A dermatoscopic image of a skin lesion.
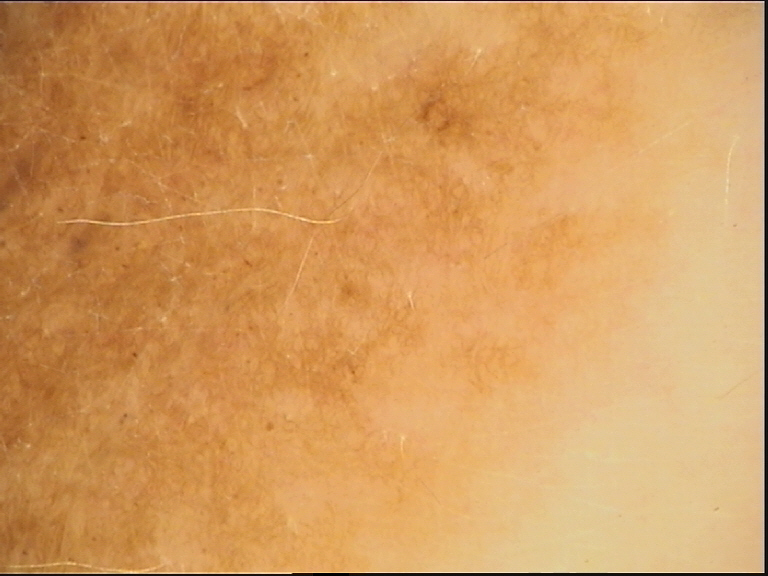category: banal; assessment: congenital junctional nevus (expert consensus).